A skin lesion imaged with a dermatoscope:
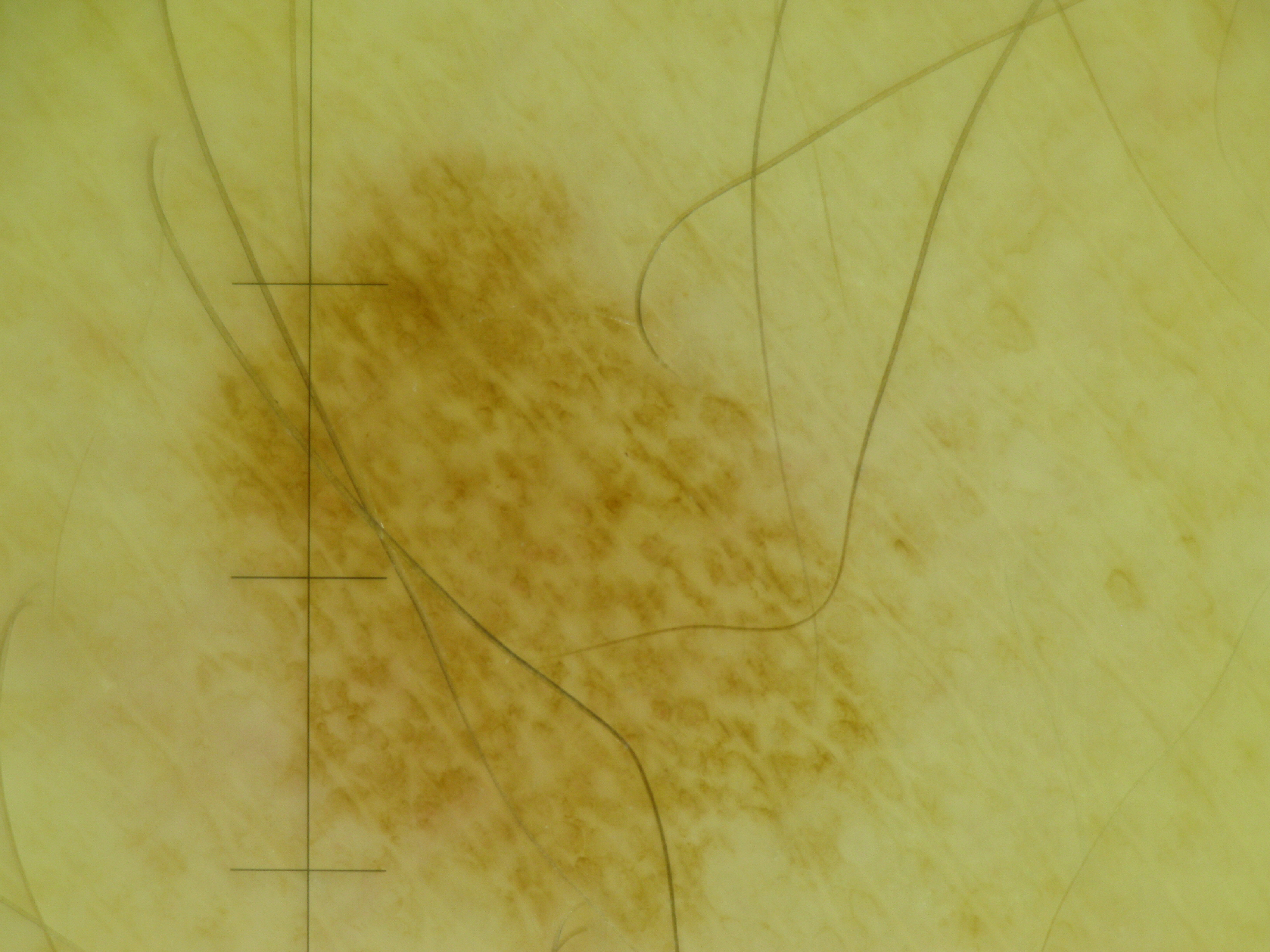Labeled as a benign lesion — a dysplastic junctional nevus.